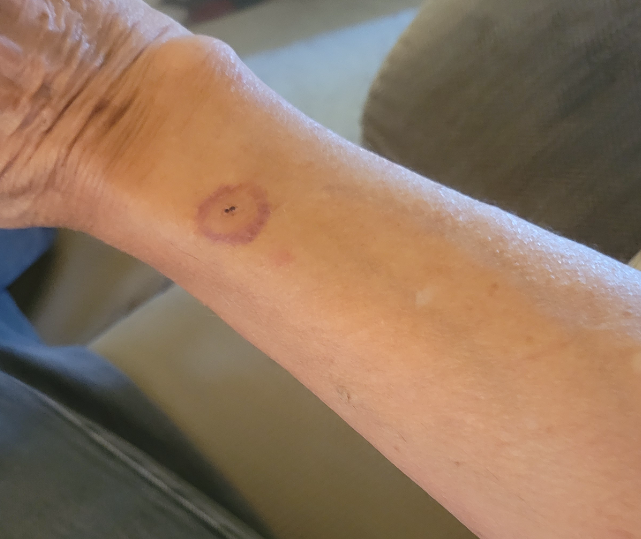- assessment: indeterminate from the photograph
- affected area: arm
- photo taken: at a distance